A dermoscopic close-up of a skin lesion.
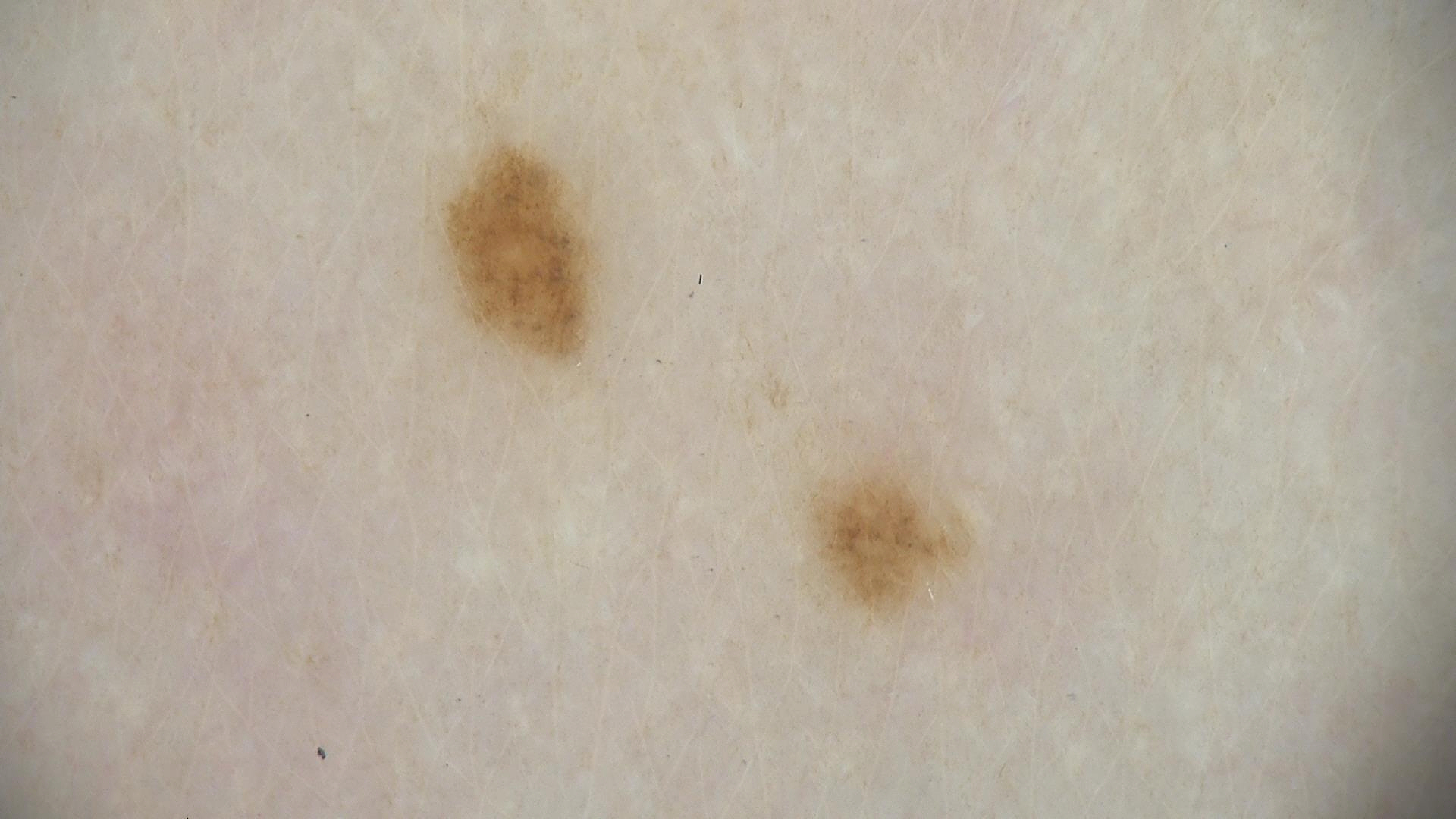Case:
The morphology is that of a banal lesion.
Impression:
Consistent with a junctional nevus.